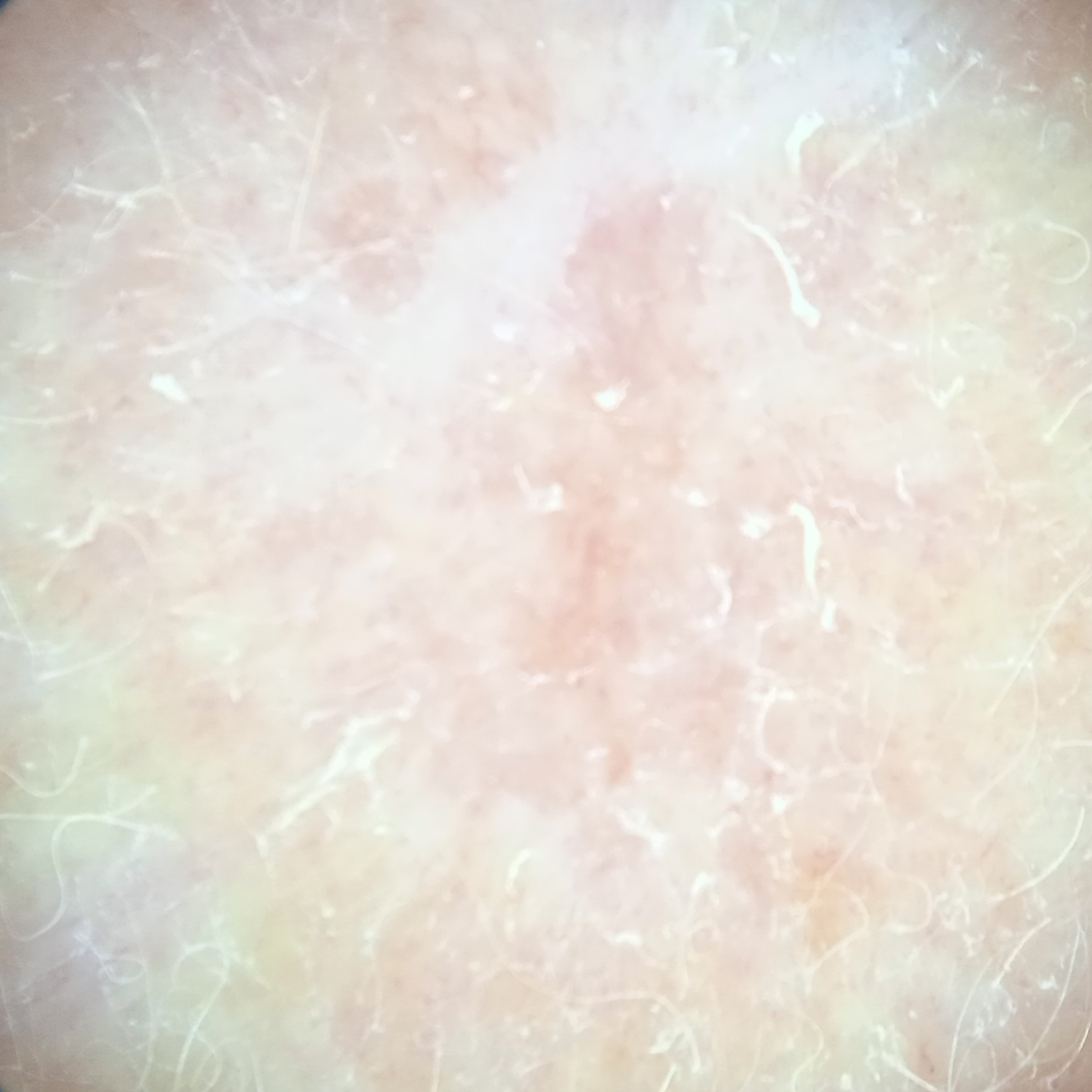sun reaction = skin tans without first burning; relevant history = a family history of skin cancer, a personal history of cancer; modality = dermatoscopic image; body site = the face; lesion size = 11.5 mm; diagnosis = basal cell carcinoma (biopsy-proven).